The photograph was taken at an angle, the lesion involves the front of the torso.
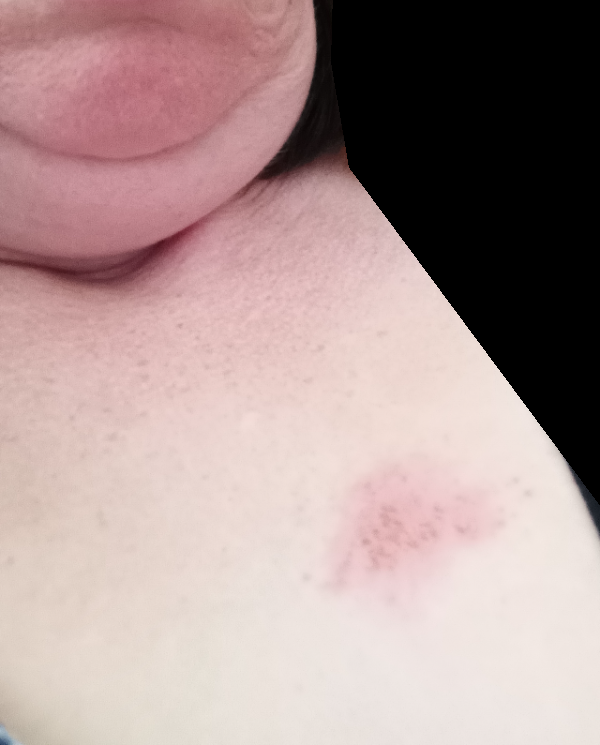The reviewing dermatologist was unable to assign a differential diagnosis from the image. Present for less than one week. Self-categorized by the patient as a rash. The patient reported no systemic symptoms. Human graders estimated Monk skin tone scale 2. The contributor reports the lesion is rough or flaky.